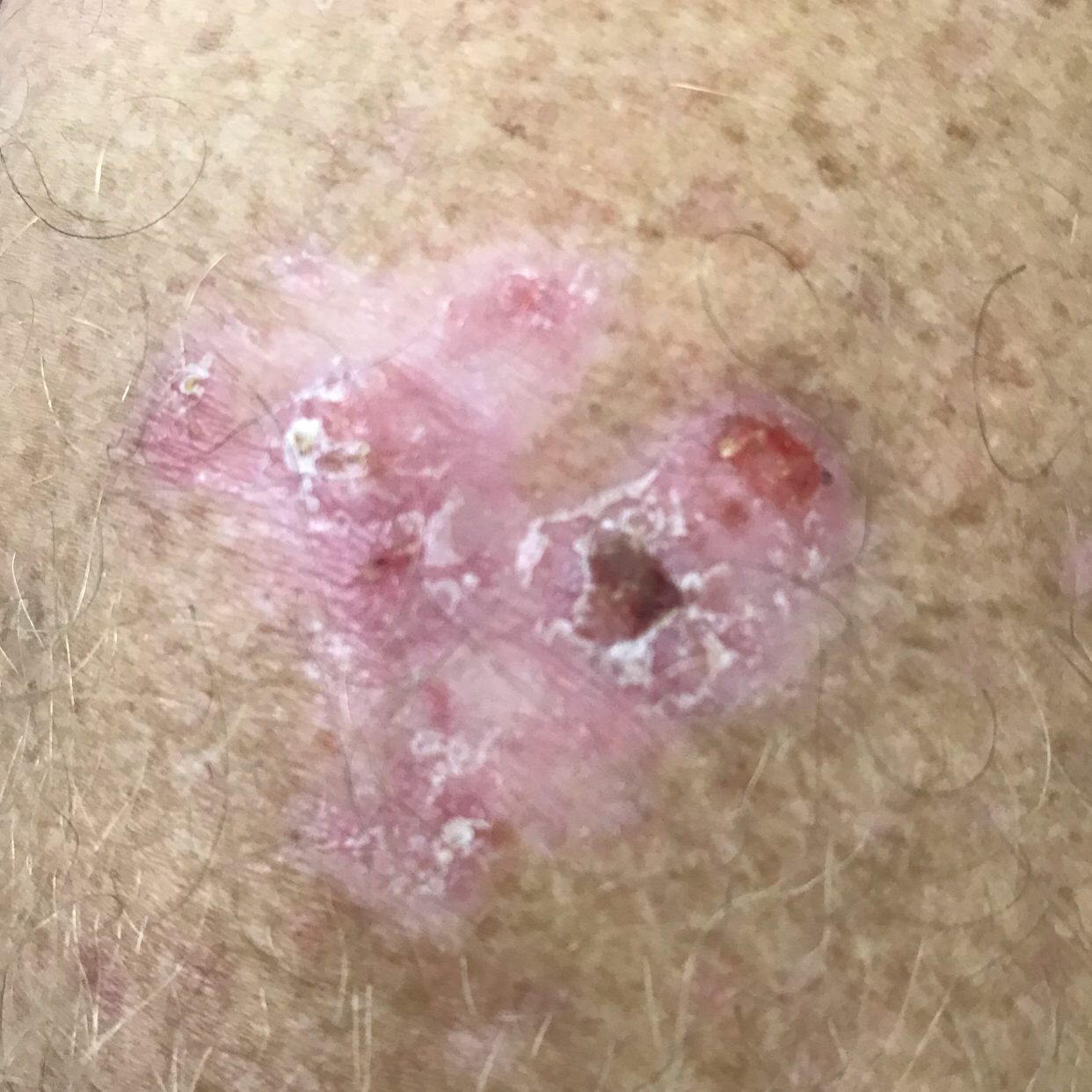Q: What is the patient's skin type?
A: II
Q: What is the imaging modality?
A: smartphone clinical photo
Q: Any relevant history?
A: tobacco use, prior skin cancer (patient or family), pesticide exposure, alcohol use
Q: Patient demographics?
A: male, 67 years of age
Q: What is the anatomic site?
A: an arm
Q: How large is the lesion?
A: approx. 40 × 34 mm
Q: What does the patient describe?
A: pain, itching, bleeding, elevation
Q: What is the diagnosis?
A: basal cell carcinoma (biopsy-proven)